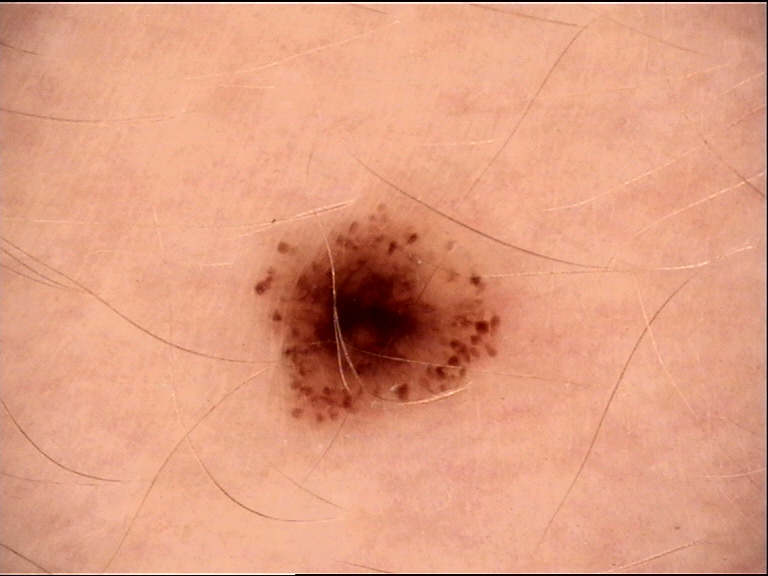The diagnosis was a dysplastic junctional nevus.